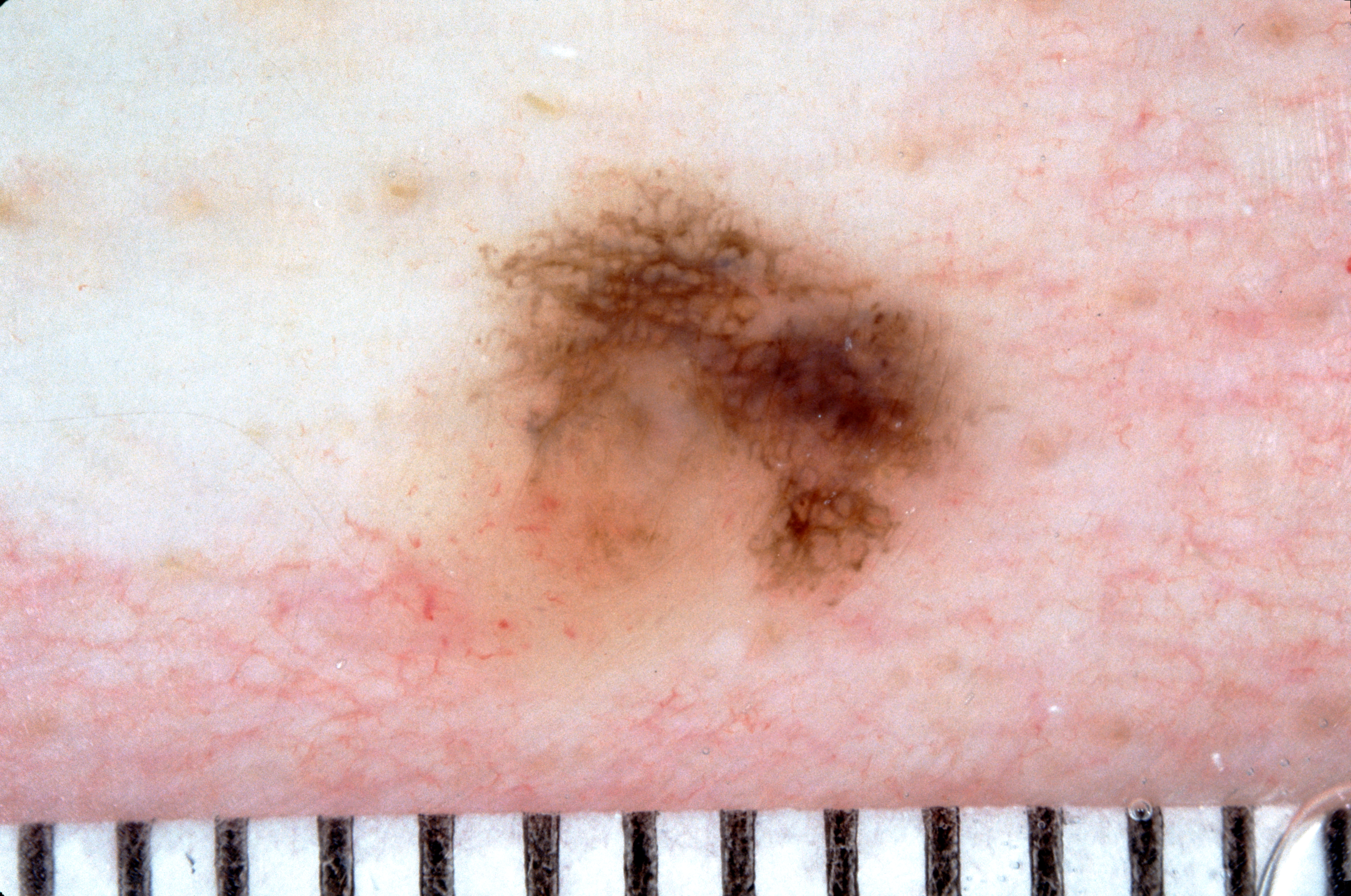The patient is a female aged approximately 40.
A dermoscopy image of a single skin lesion.
In (x1, y1, x2, y2) order, the lesion's extent is <bbox>319, 165, 1025, 727</bbox>.
Dermoscopic assessment notes pigment network.
The clinical diagnosis was a melanocytic nevus.